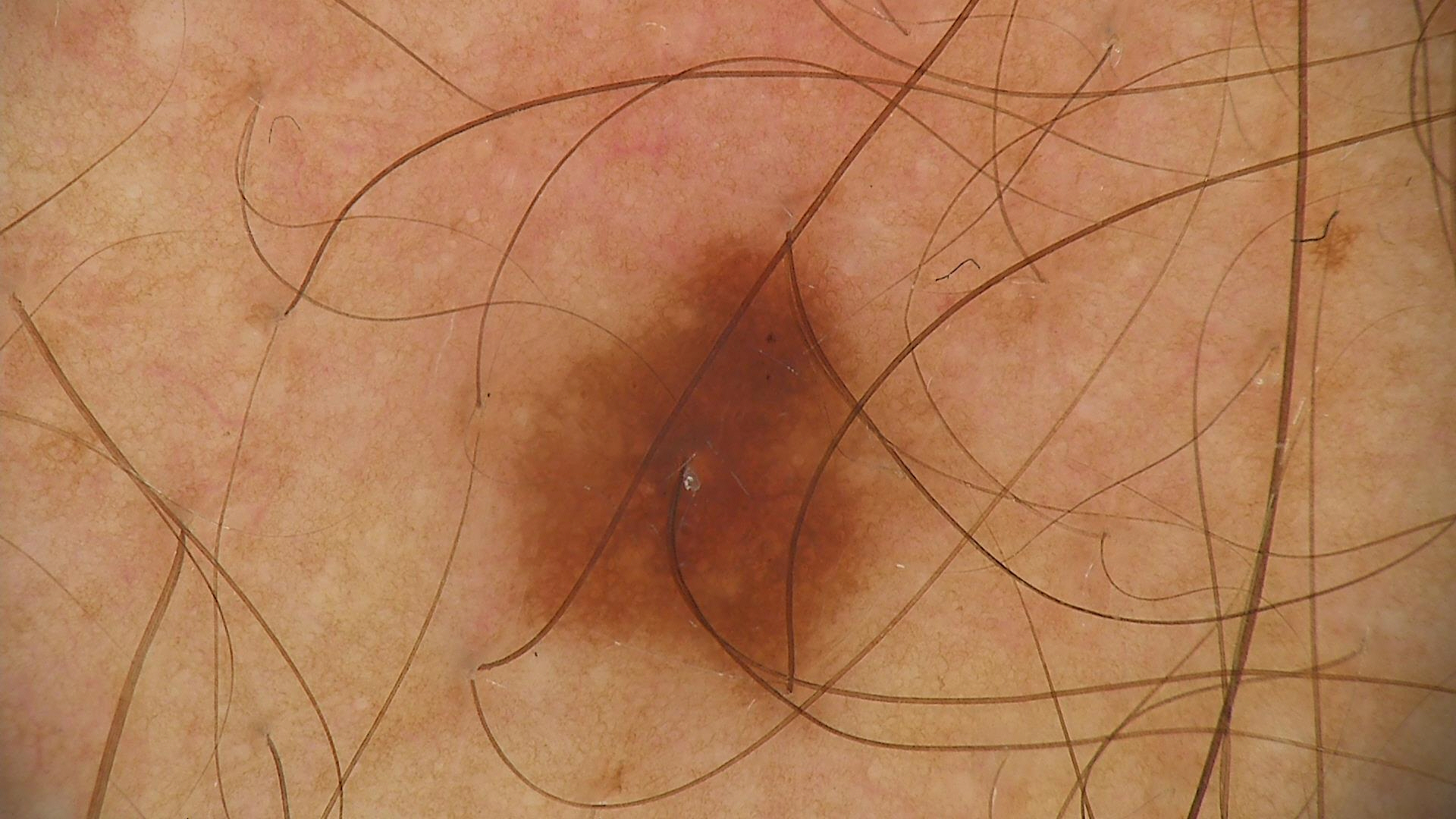Diagnosed as a dysplastic junctional nevus.